The contributor is 18–29, female · the photograph was taken at a distance · the affected area is the arm and leg — 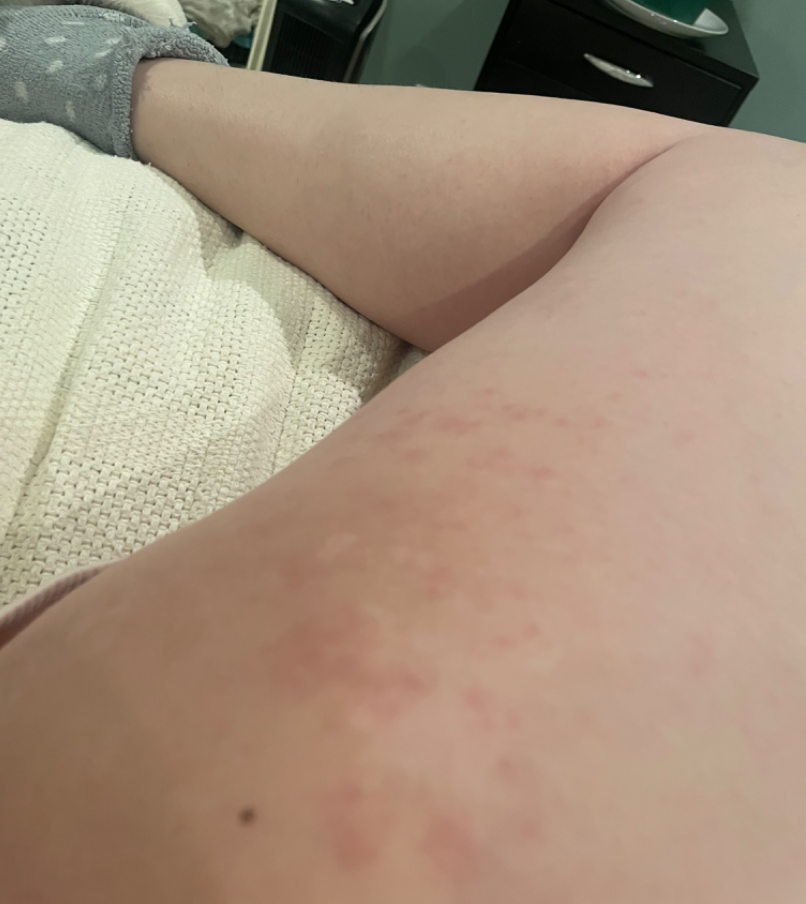{
  "symptoms": "itching",
  "duration": "less than one week",
  "patient_category": "a rash",
  "differential": {
    "tied_lead": [
      "Eczema",
      "Allergic Contact Dermatitis"
    ],
    "considered": [
      "Drug Rash"
    ]
  }
}